The photograph is a close-up of the affected area: 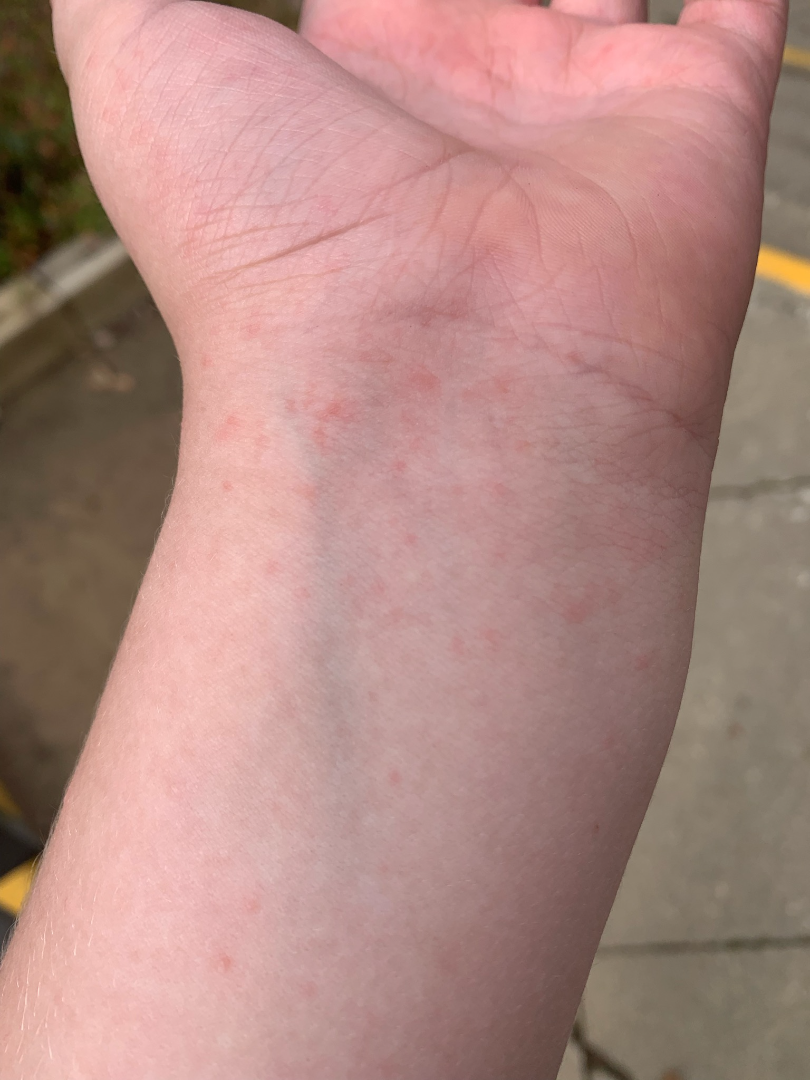assessment = not assessable.